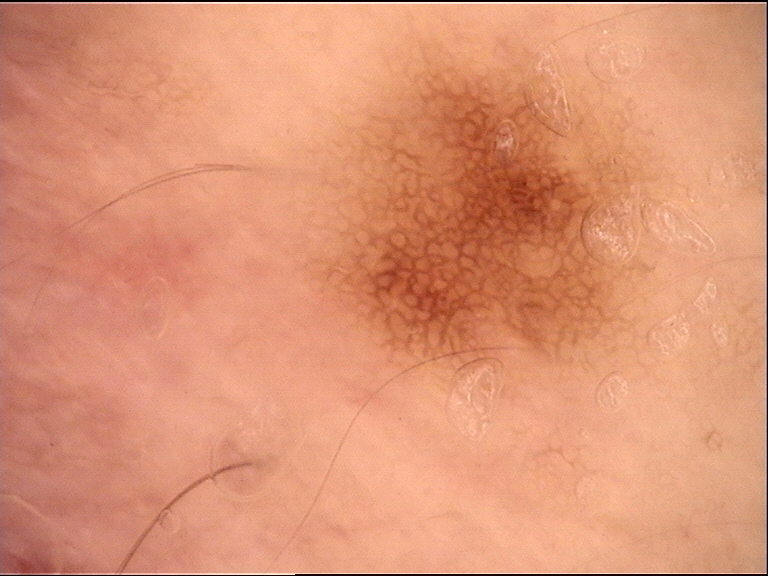| key | value |
|---|---|
| modality | dermoscopy |
| assessment | dysplastic junctional nevus (expert consensus) |